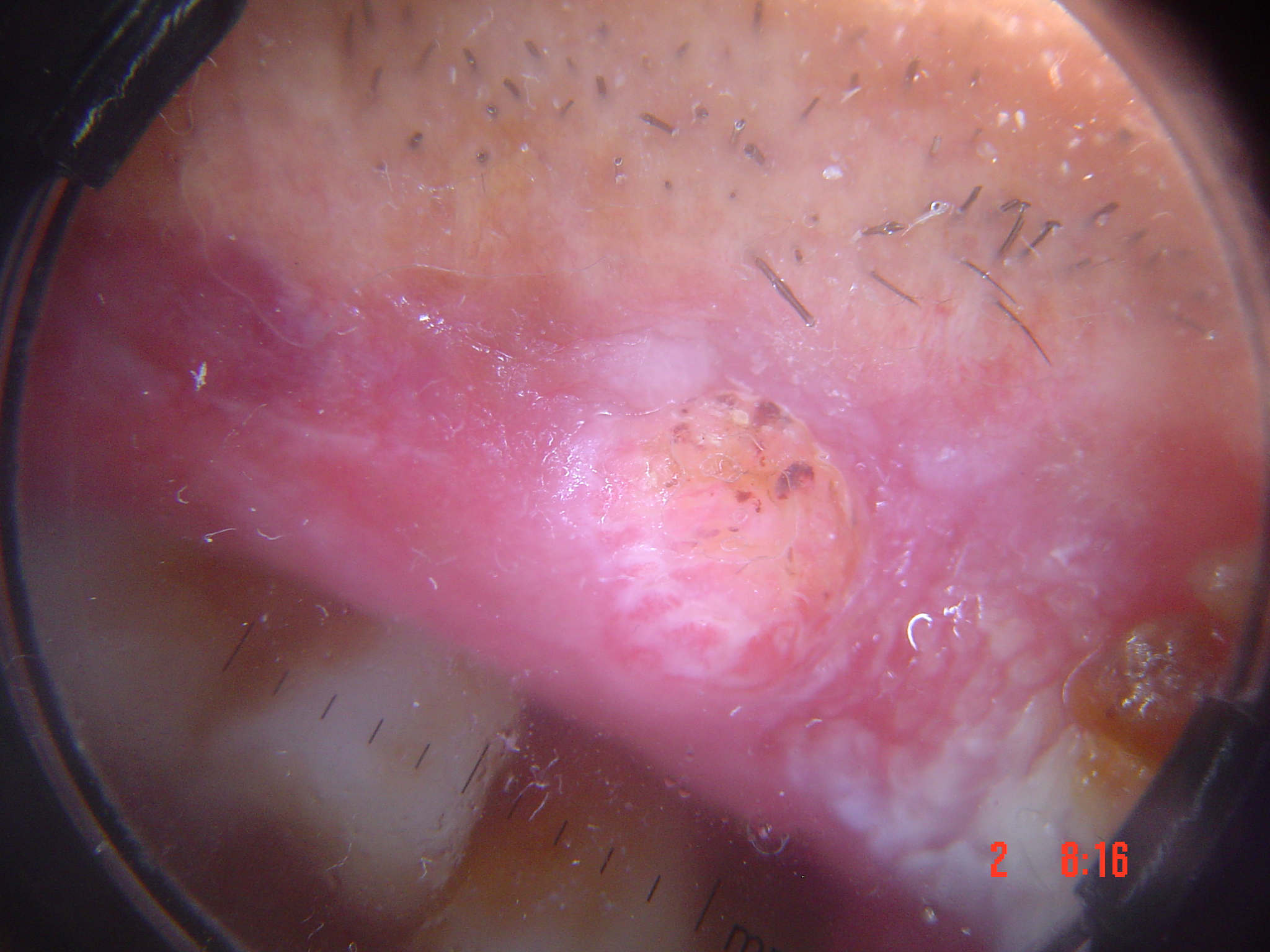The biopsy diagnosis was a keratinocytic lesion — a squamous cell carcinoma.